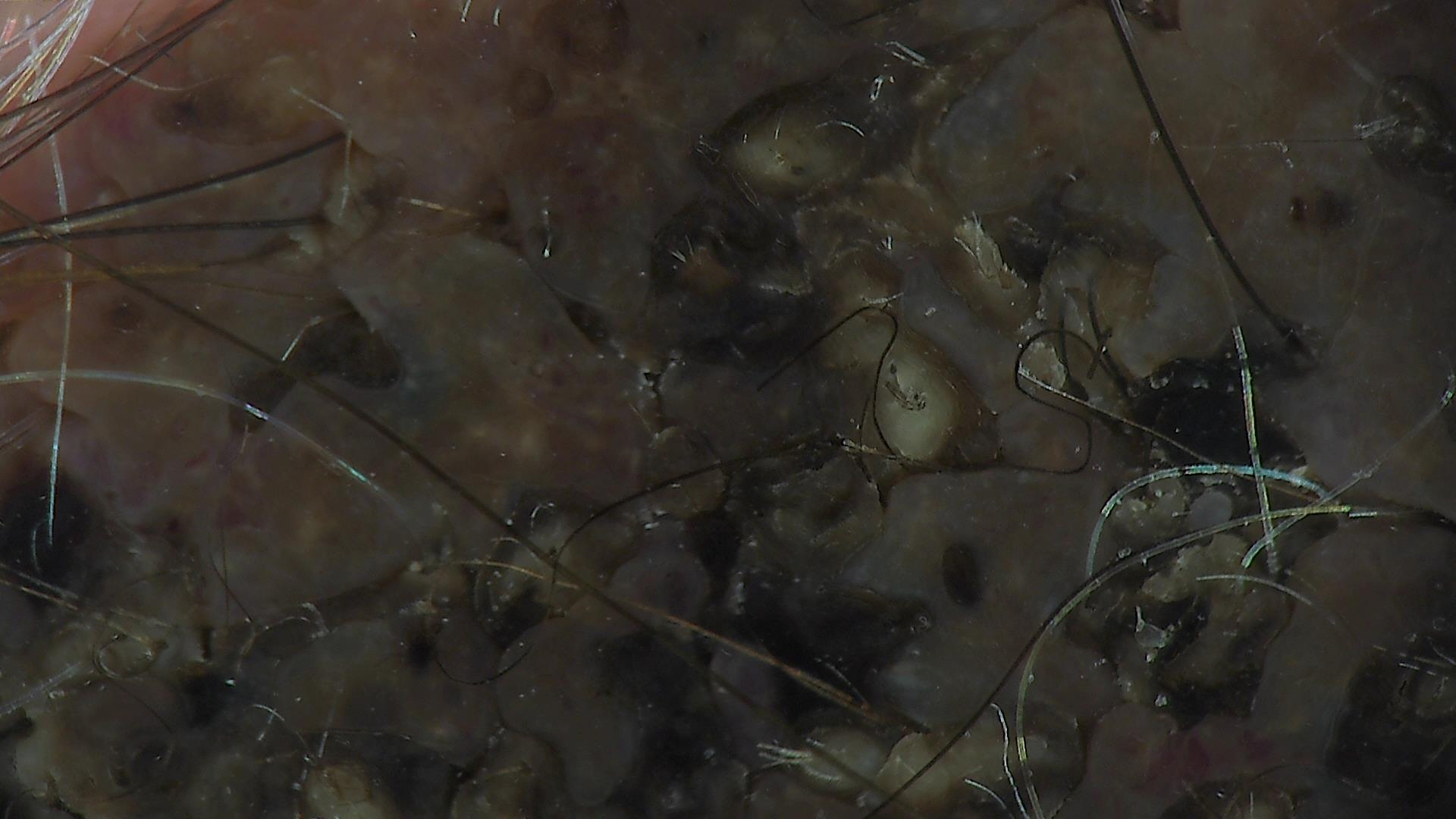A dermatoscopic image of a skin lesion.
The morphology is that of a banal lesion.
The diagnostic label was a congenital compound nevus.